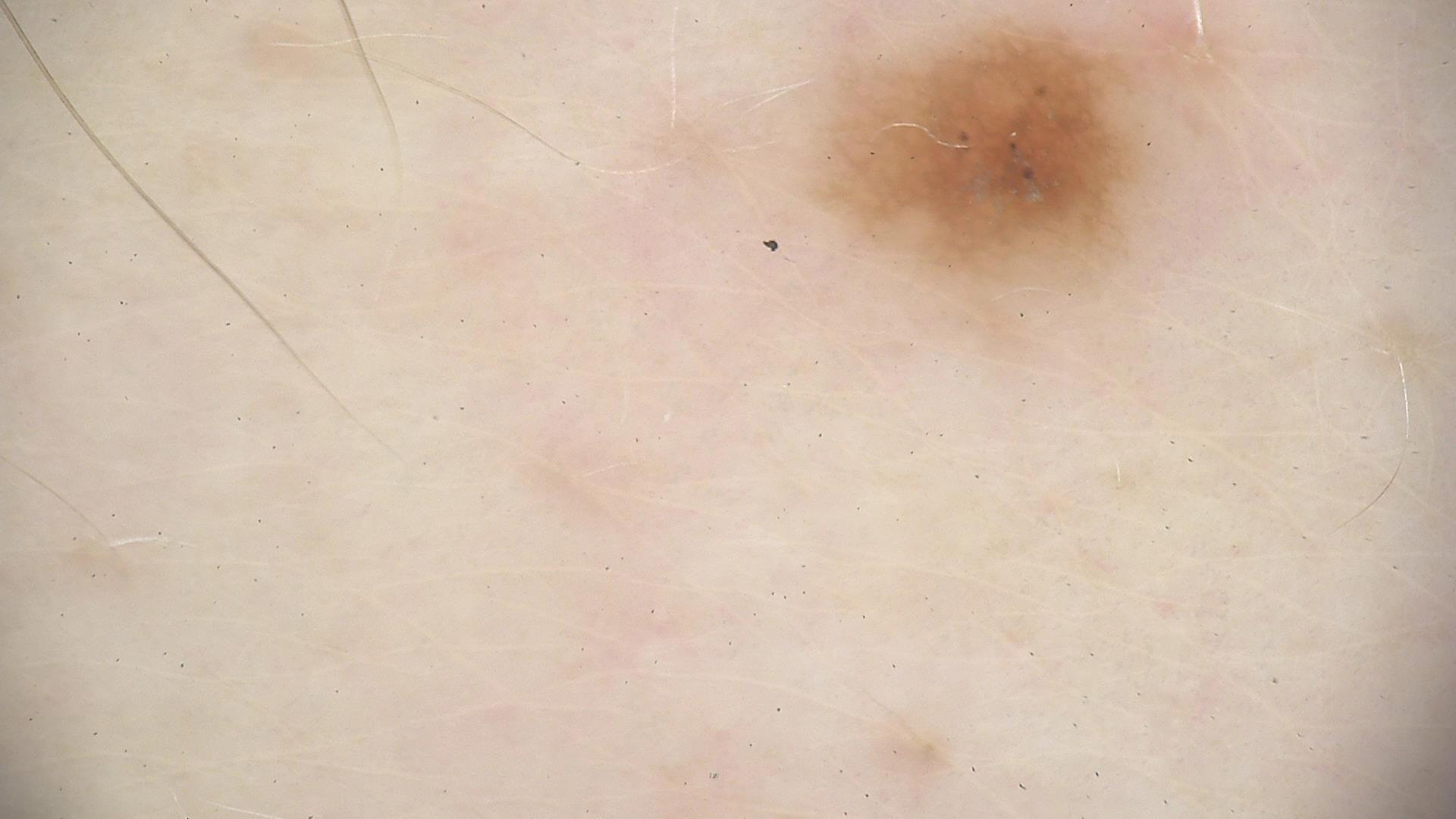A dermatoscopic image of a skin lesion.
Diagnosed as a dysplastic junctional nevus.